A skin lesion imaged with a dermatoscope: 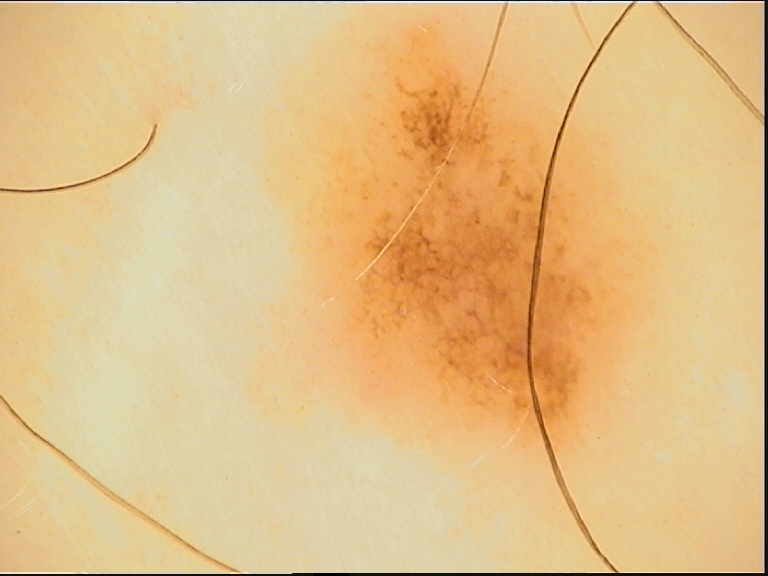Q: What was the diagnostic impression?
A: dysplastic junctional nevus (expert consensus)